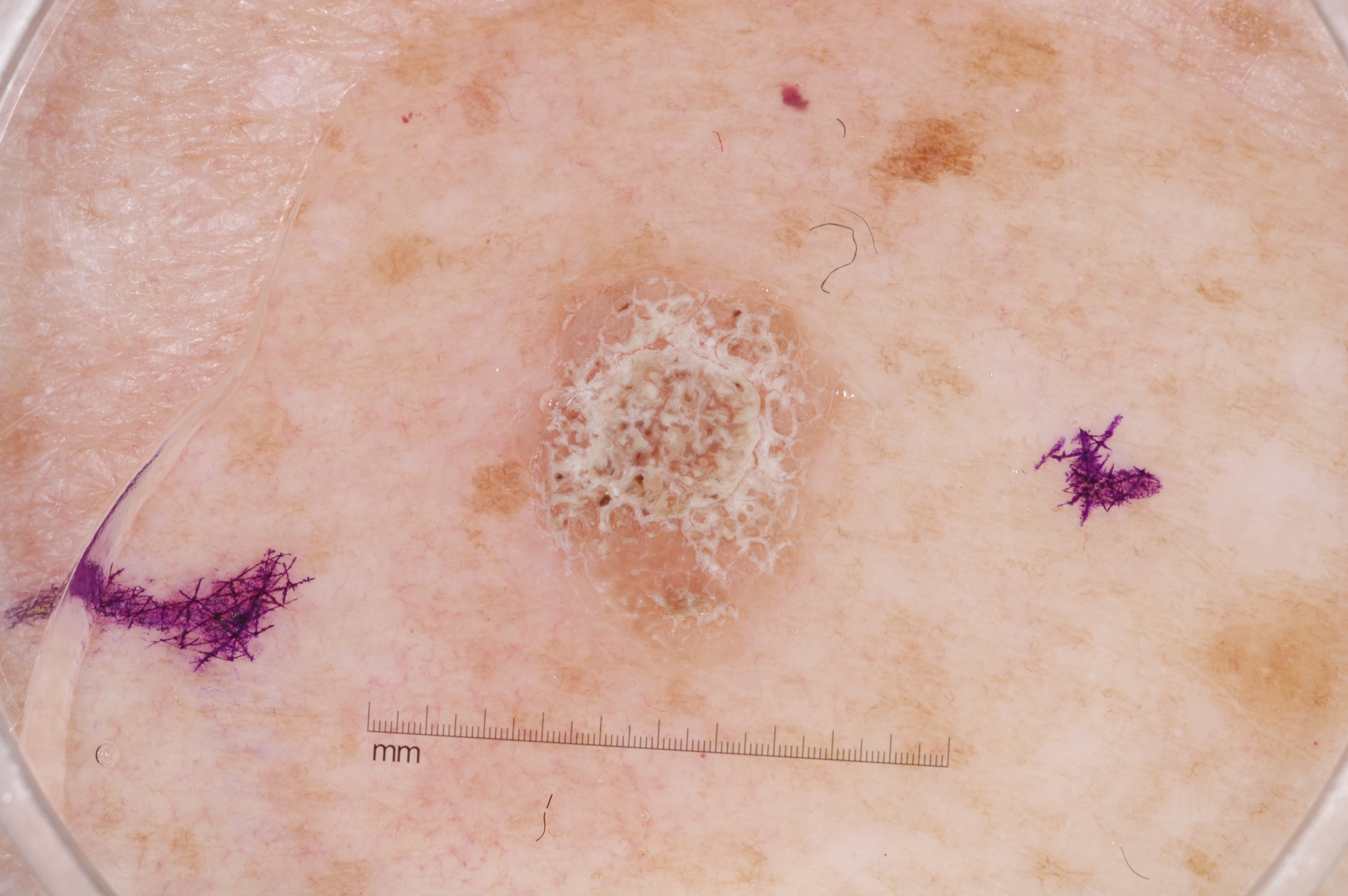Summary:
The patient is a female roughly 50 years of age. A dermoscopic image of a skin lesion. Lesion location: x1=493 y1=259 x2=861 y2=673. On dermoscopy, the lesion shows no streaks, negative network, pigment network, or milia-like cysts.
Conclusion:
Consistent with a seborrheic keratosis, a benign lesion.